A dermoscopic image of a skin lesion: 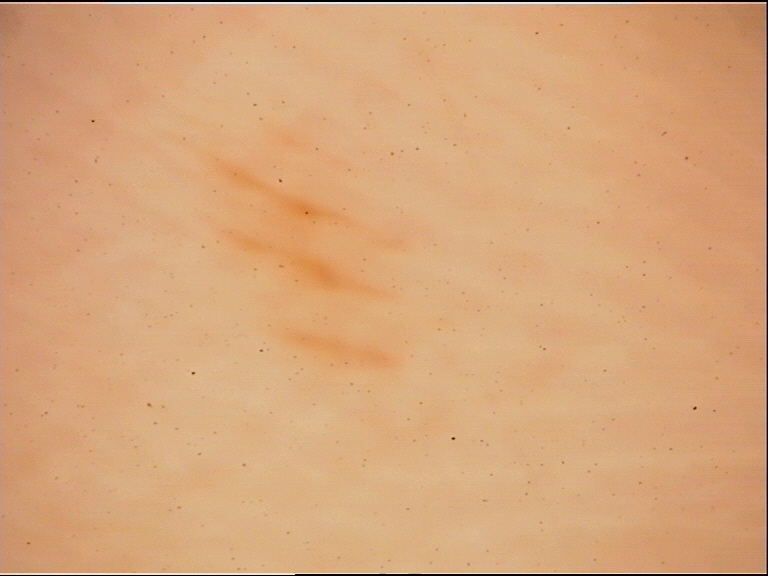The architecture is that of a banal lesion.
The diagnosis was an acral junctional nevus.